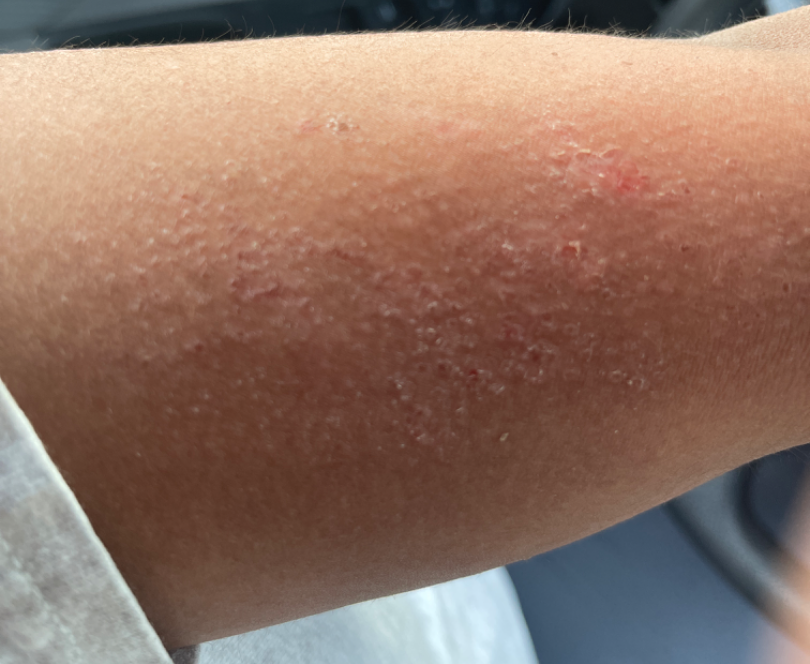<summary>
  <differential>
    <Eczema>0.54</Eczema>
    <Psoriasis>0.23</Psoriasis>
    <Lichen Simplex Chronicus>0.23</Lichen Simplex Chronicus>
  </differential>
</summary>